Collected as part of a research study, without a referral diagnosis. A female subject age 54. By self-report, a family history of skin cancer, a personal history of cancer, and a personal history of skin cancer. The patient says their skin reddens with sun exposure. Numerous moles by the patient's own estimate. A clinical photograph of a skin lesion — 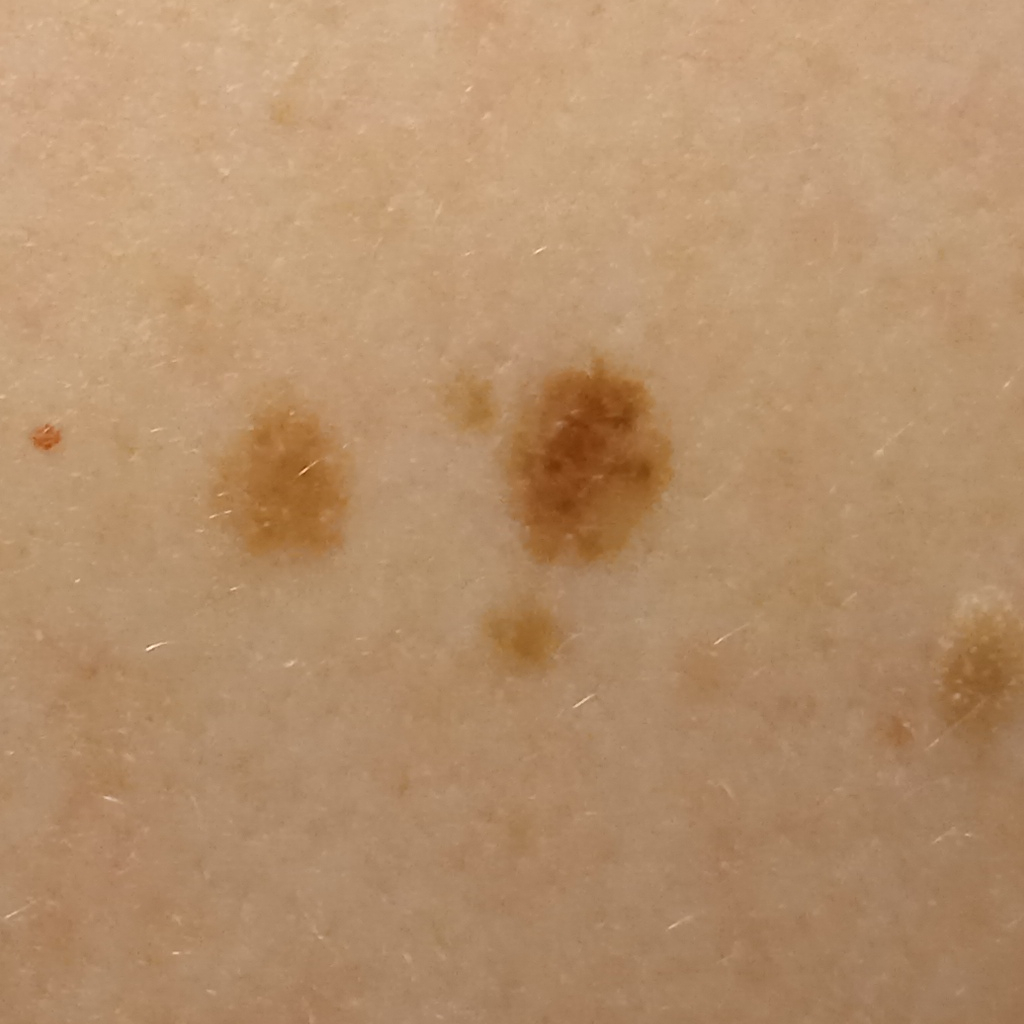Measuring roughly 6.4 mm. The consensus diagnosis for this lesion was an atypical (dysplastic) nevus.